Close-up view, the head or neck is involved — 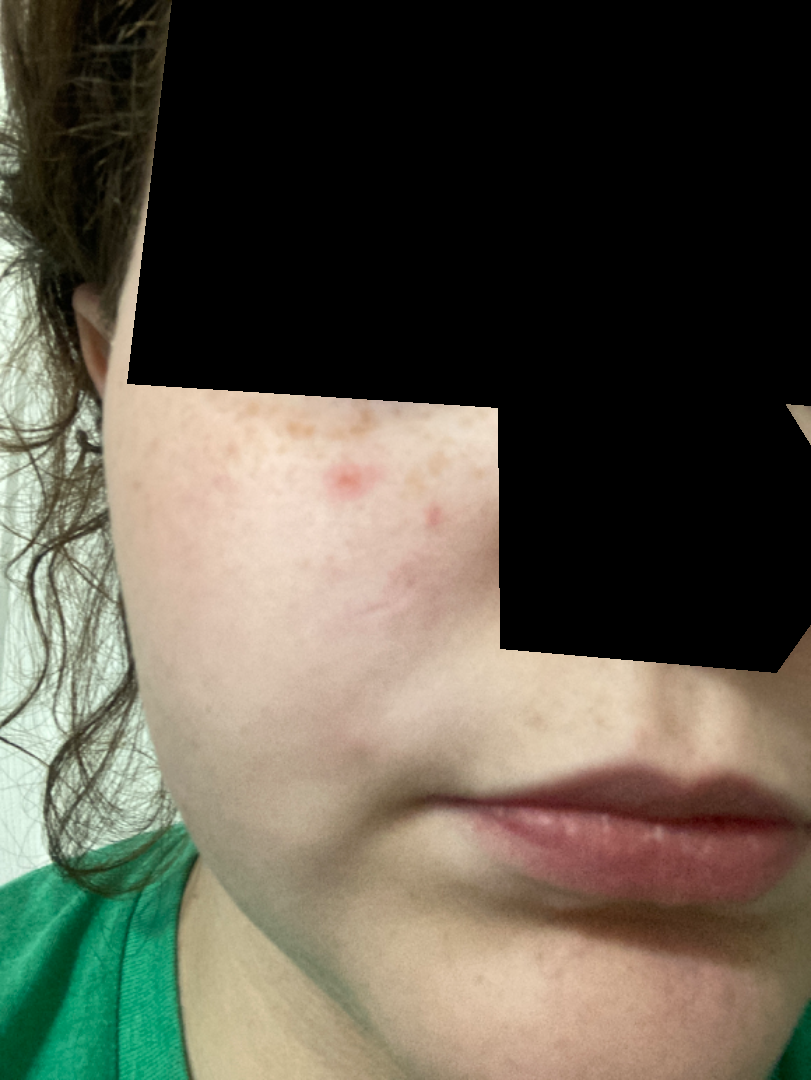Diagnostic features were not clearly distinguishable in this photograph. No constitutional symptoms were reported. Self-categorized by the patient as a rash. The patient notes the lesion is rough or flaky. The condition has been present for less than one week. The lesion is associated with bothersome appearance. Skin tone: Fitzpatrick skin type III; lay reviewers estimated a Monk Skin Tone of 2.